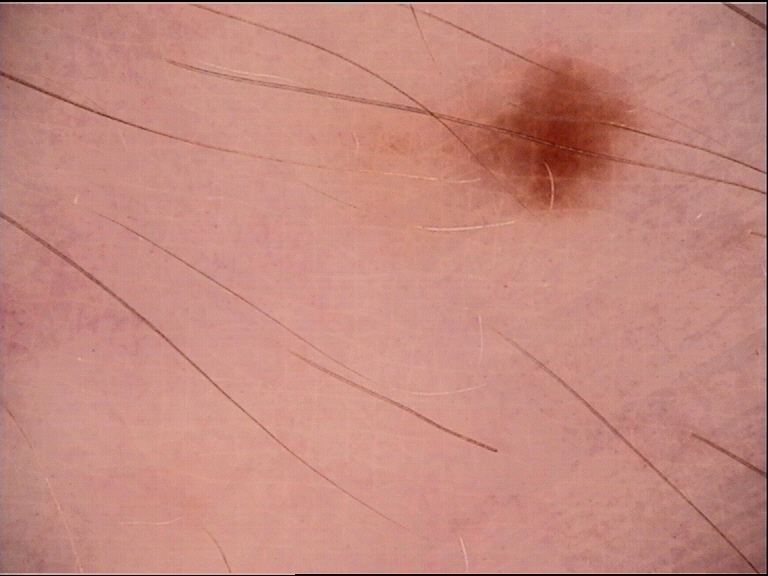imaging — dermoscopy; subtype — banal; diagnostic label — junctional nevus (expert consensus).